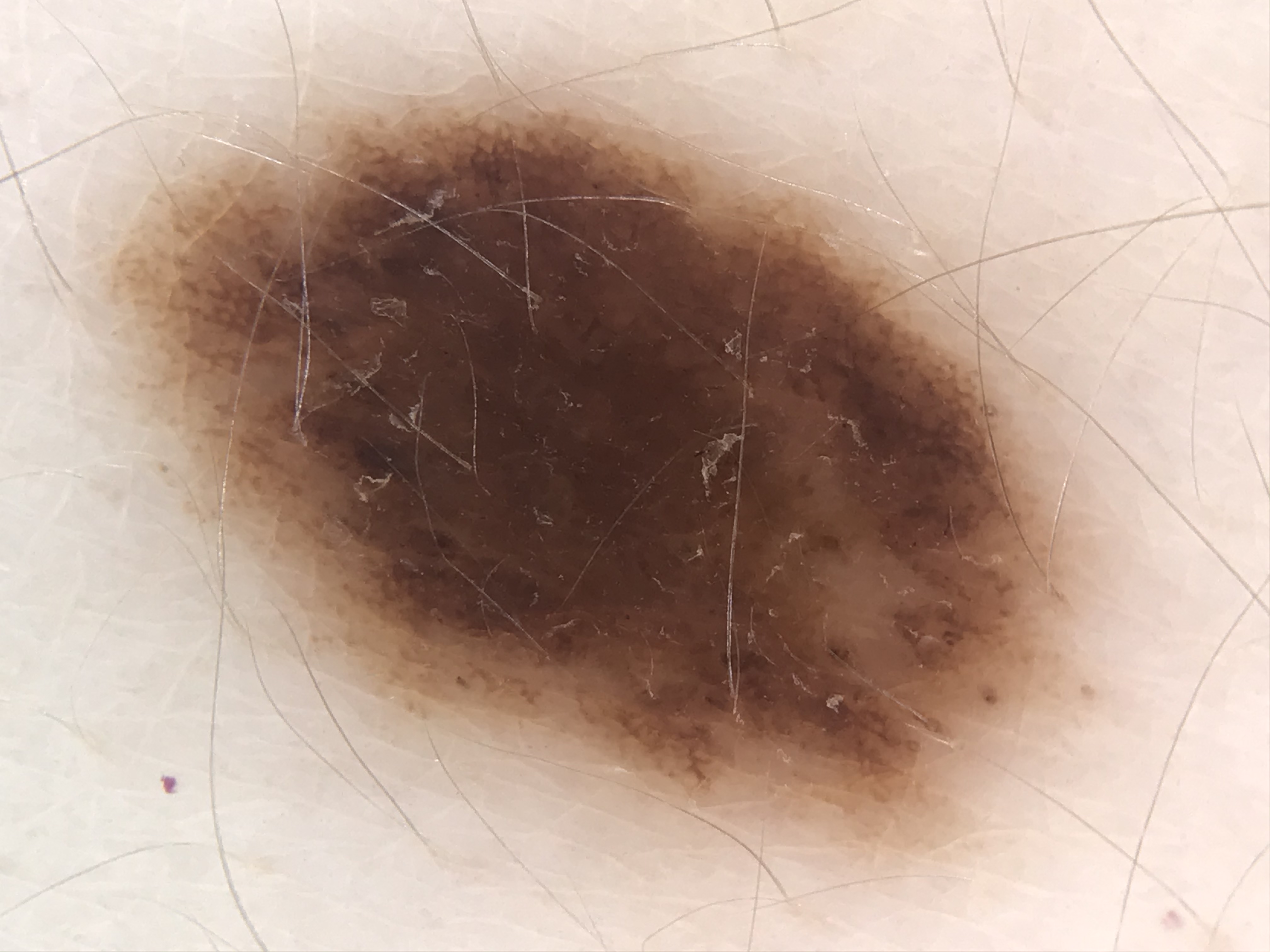The diagnosis was a dysplastic compound nevus.